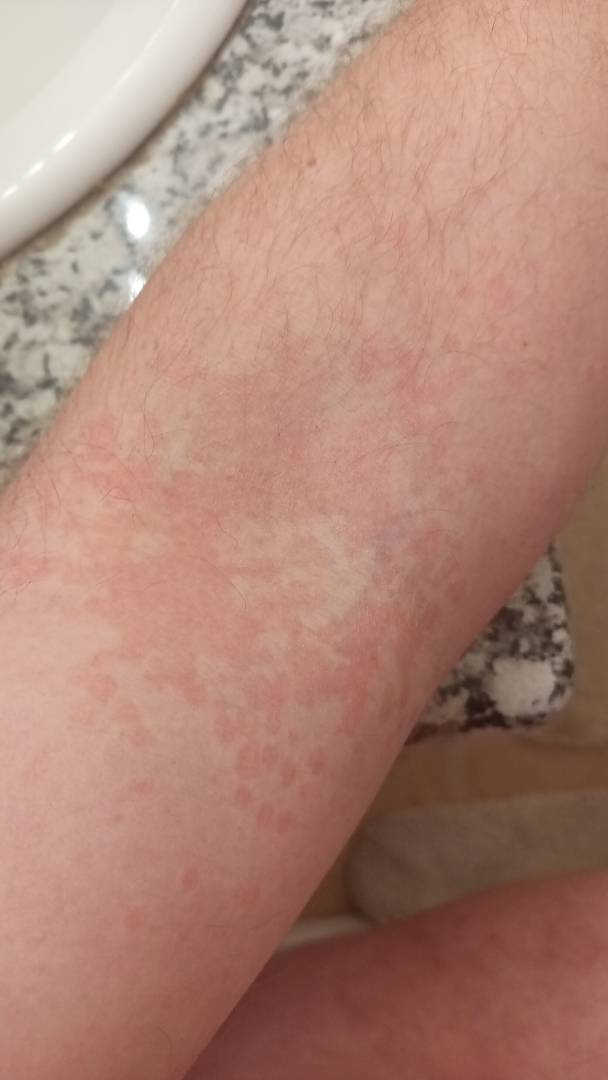<report>
  <assessment>ungradable on photographic review</assessment>
  <shot_type>close-up</shot_type>
</report>